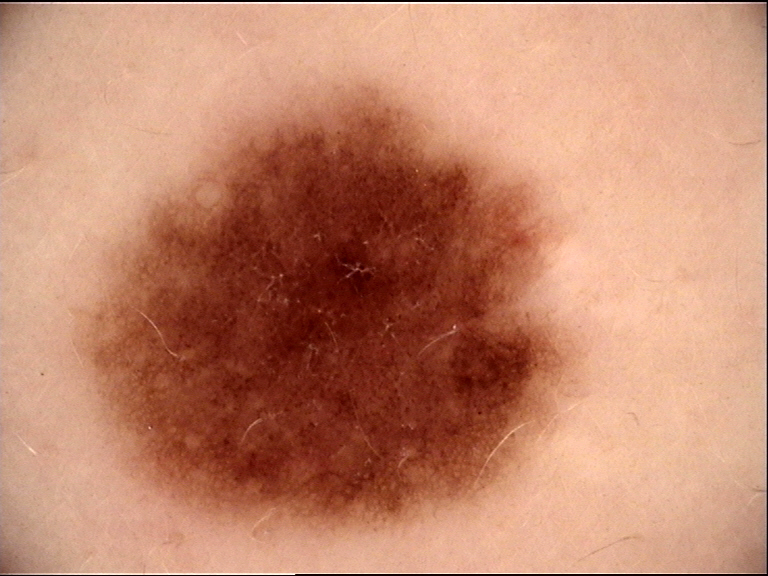Summary:
Dermoscopy of a skin lesion.
Impression:
Diagnosed as a dysplastic junctional nevus.